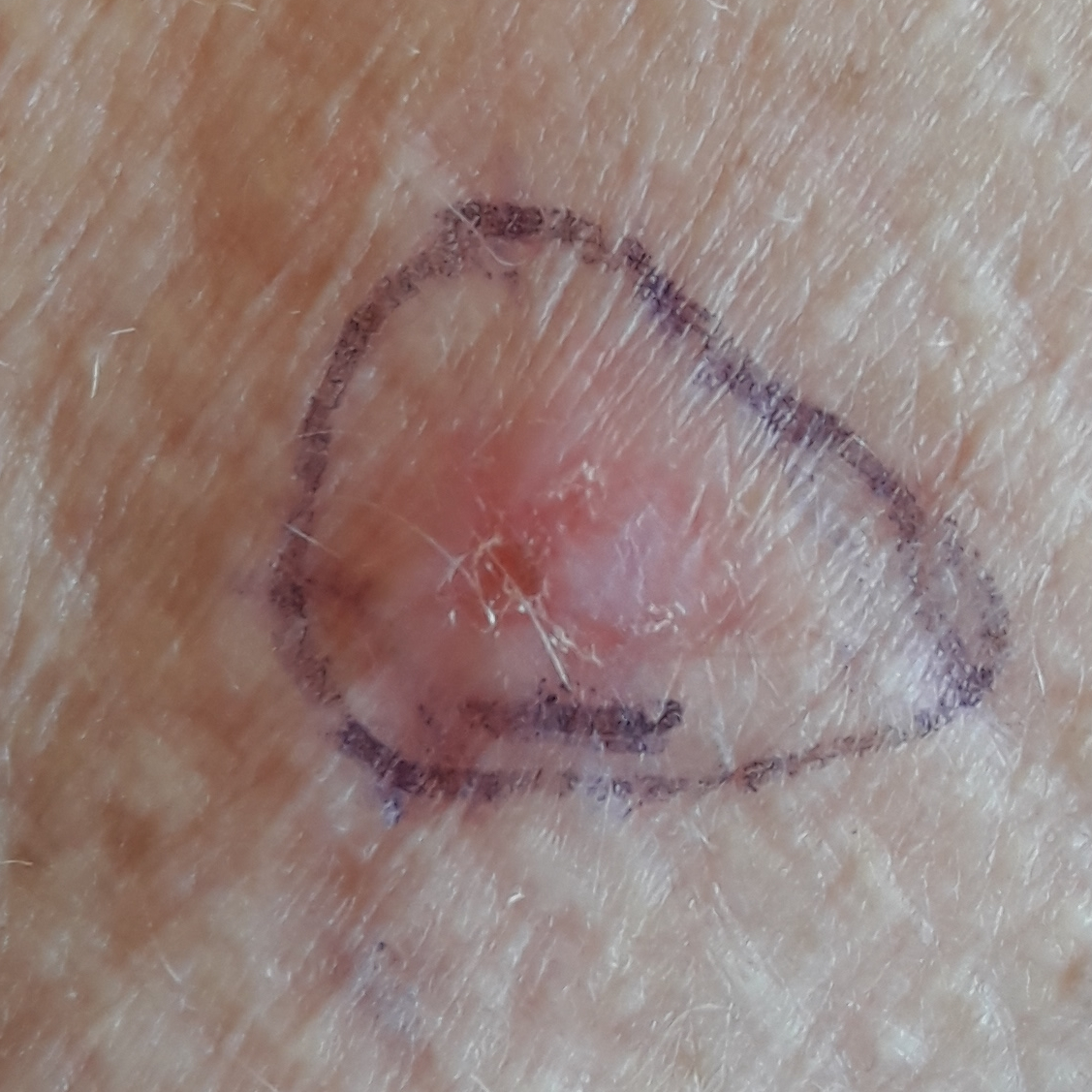A female subject age 67. A clinical photo of a skin lesion taken with a smartphone. The lesion is located on a forearm. The patient reports that the lesion has grown and is elevated. Histopathological examination showed a basal cell carcinoma.